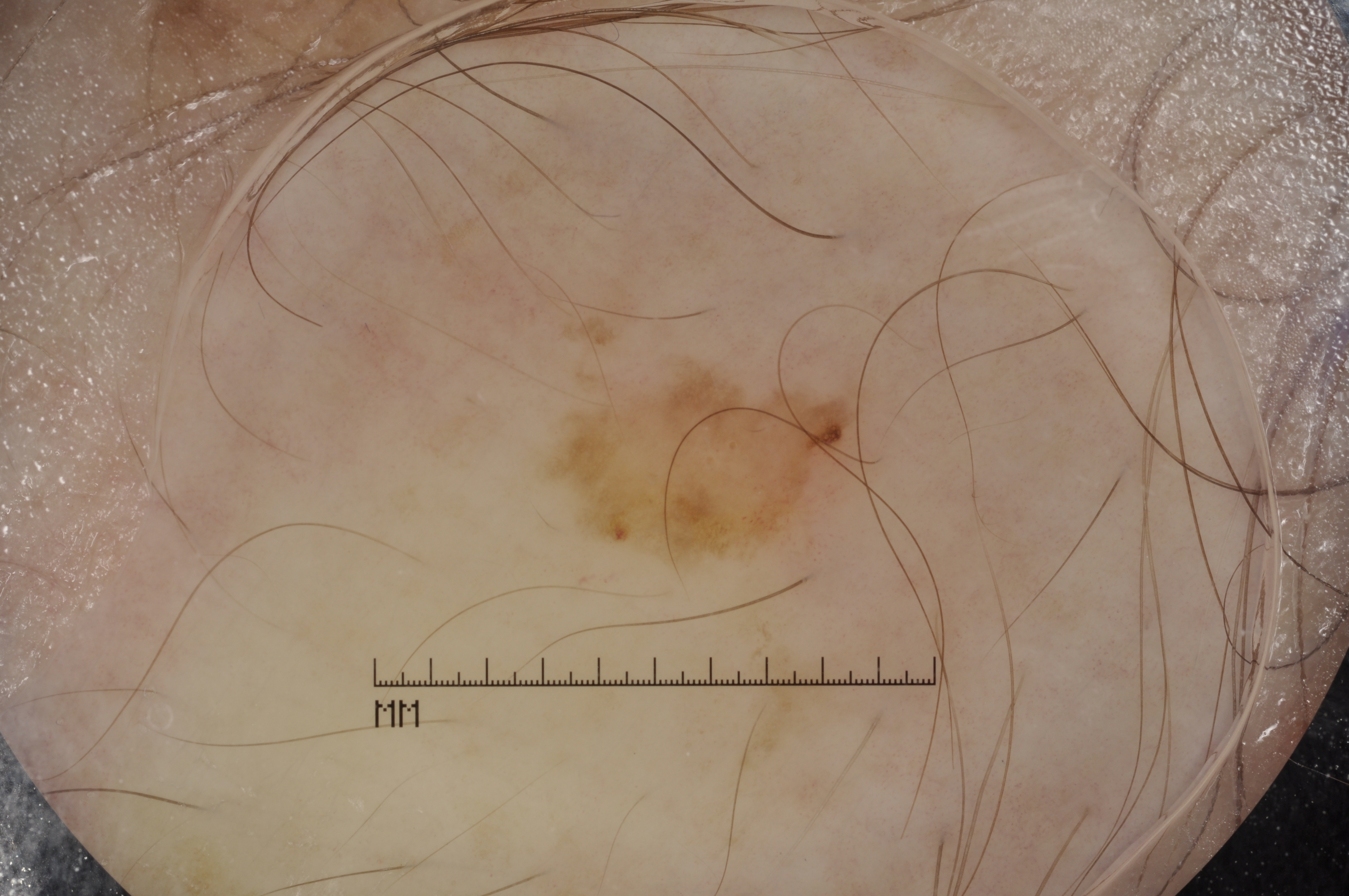patient: male, aged around 60; modality: dermoscopic image; lesion bbox: [559, 378, 864, 553]; dermoscopic features assessed but absent: milia-like cysts, pigment network, negative network, and streaks; extent: small; assessment: a seborrheic keratosis.